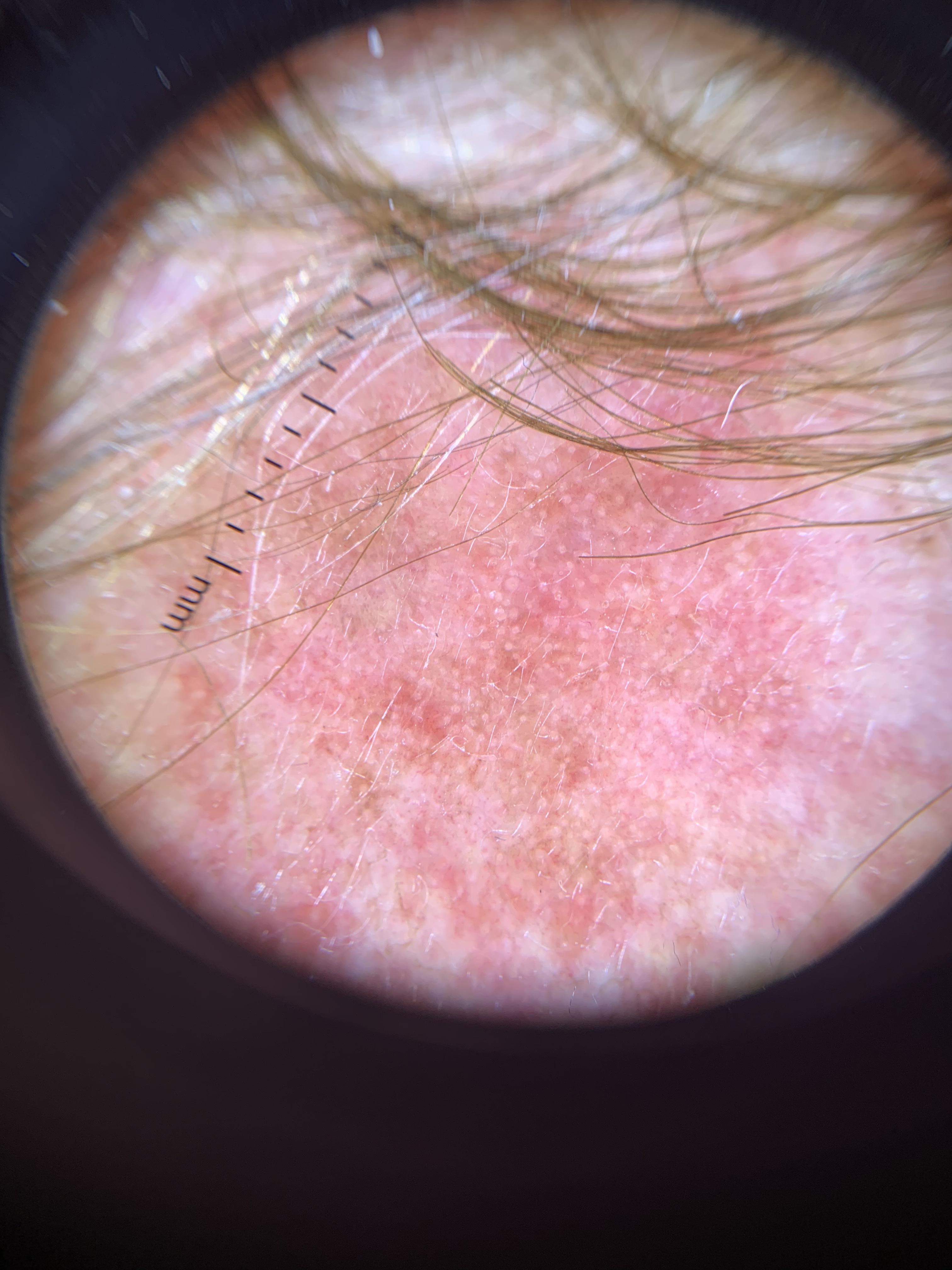Assessment:
Consistent with a solar or actinic keratosis.